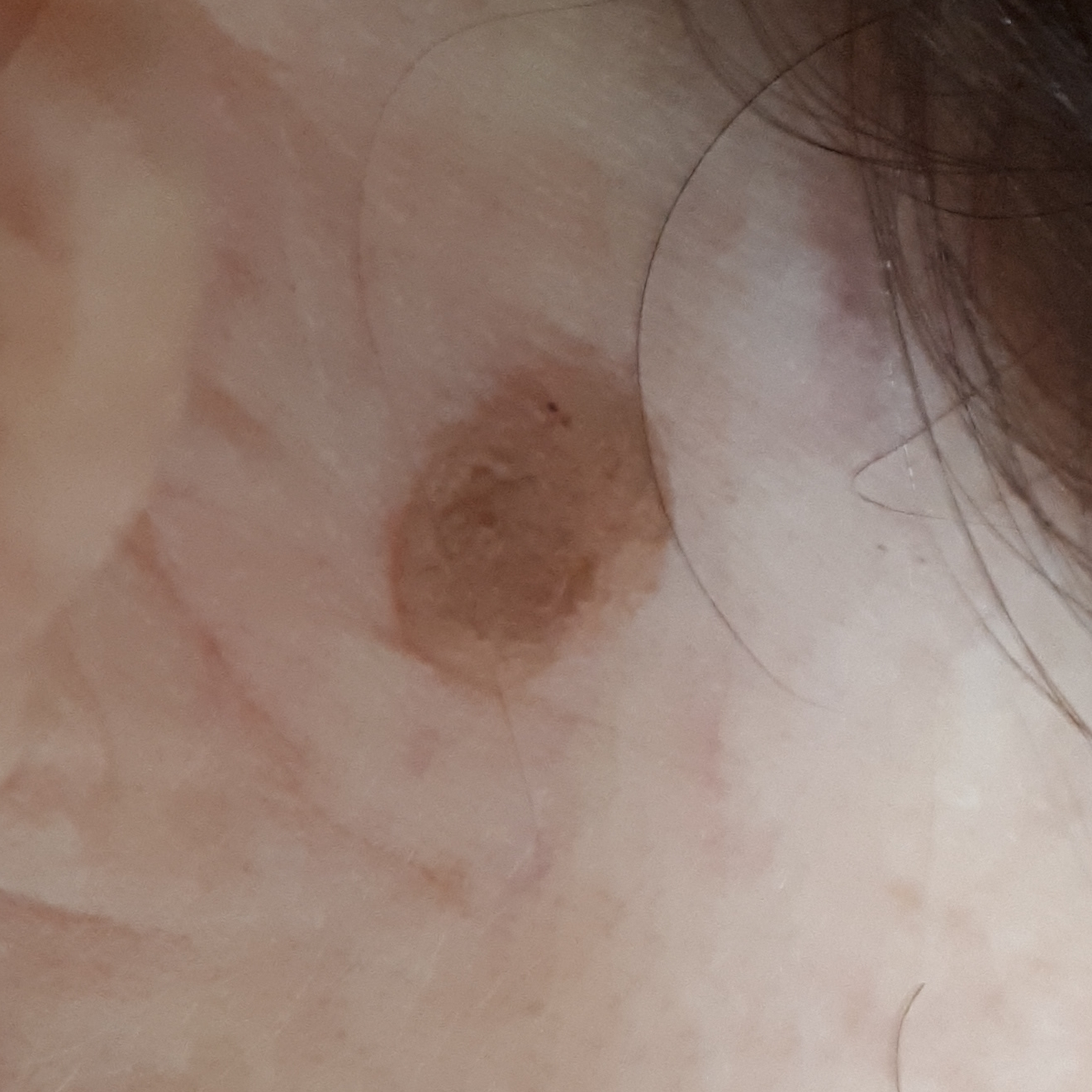• image type · smartphone clinical photo
• subject · female, age 87
• skin phototype · II
• site · the face
• lesion diameter · 5 × 4 mm
• patient-reported symptoms · growth, elevation / no pain, no change in appearance
• impression · seborrheic keratosis (clinical consensus)